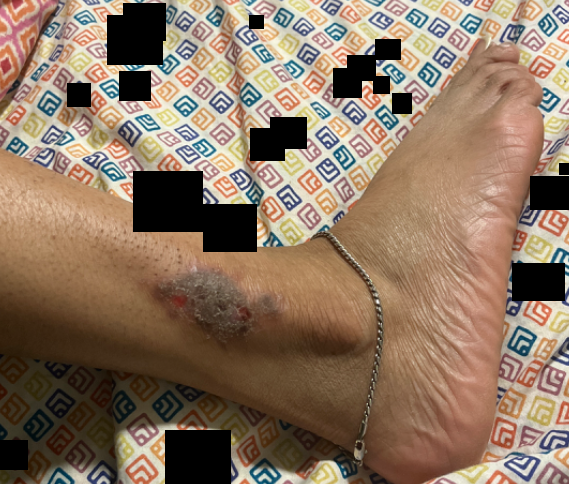Q: What is the dermatologist's impression?
A: three independent reviewers: the favored diagnosis is Lichen Simplex Chronicus; also consider Mycetoma; a more distant consideration is Deep fungal infection; less probable is Lichen planus/lichenoid eruption